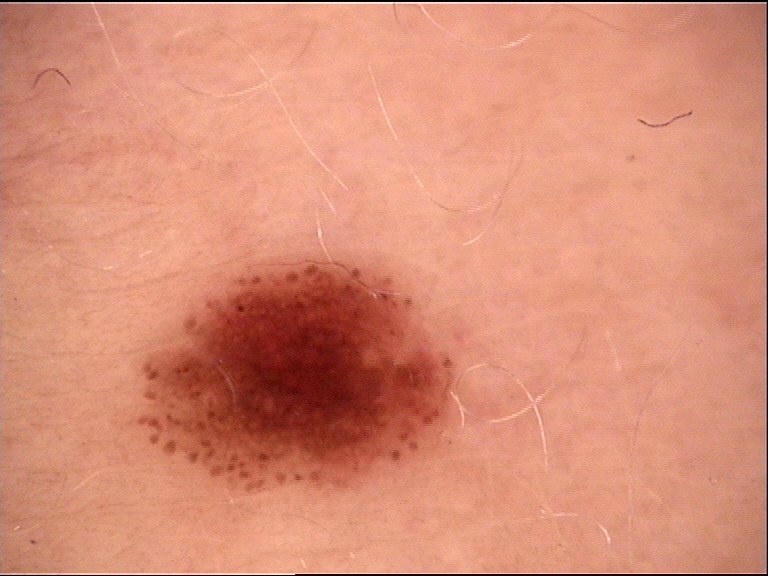Q: What kind of image is this?
A: dermoscopy
Q: What is the diagnosis?
A: dysplastic junctional nevus (expert consensus)